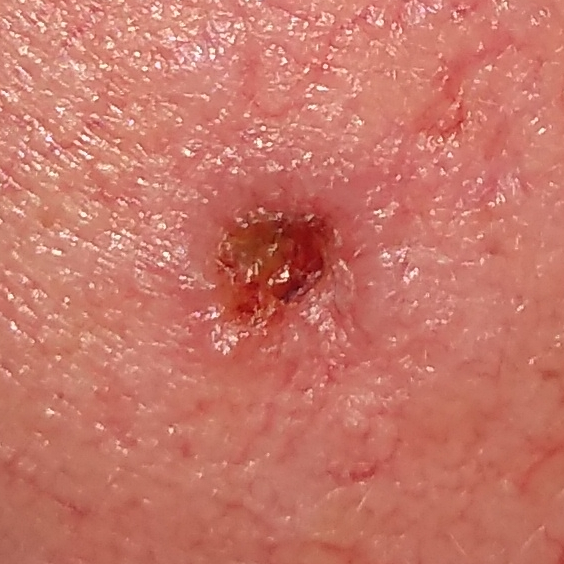A clinical photograph showing a skin lesion.
The chart notes alcohol use and prior malignancy (patient or family).
A male subject 77 years of age.
The patient was assessed as Fitzpatrick skin type I.
The lesion is located on the face.
Measuring about 6 × 5 mm.
By the patient's account, the lesion itches.
Confirmed on histopathology as a malignant skin lesion — a basal cell carcinoma.